The lesion involves the front of the torso, head or neck and arm. The photograph was taken at an angle. Male subject, age 40–49.
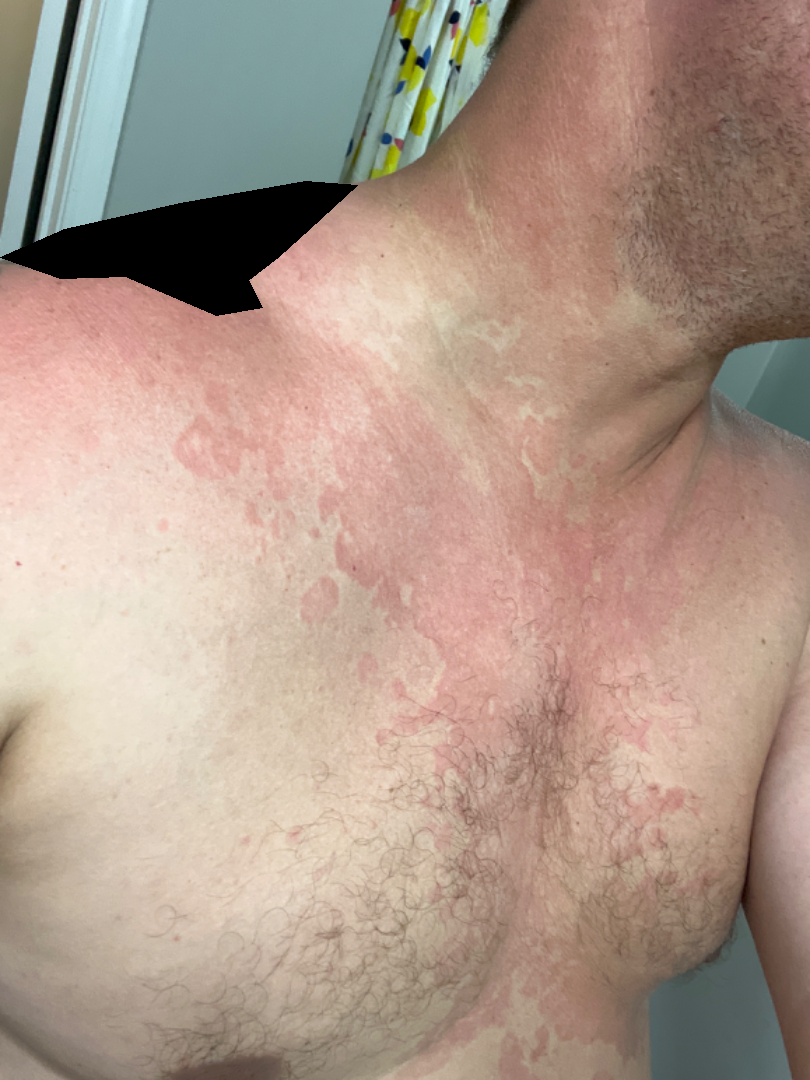constitutional symptoms = none reported
history = more than five years
lesion texture = raised or bumpy
lesion symptoms = bothersome appearance, enlargement and itching
skin tone = Fitzpatrick skin type III
diagnostic considerations = three dermatologists each reviewed the case: favoring Tinea Versicolor; less probable is Drug-induced pellagra; lower on the differential is Eczema